Close-up view. Present for less than one week. Texture is reported as raised or bumpy. The lesion involves the head or neck. The patient is a male aged 50–59. The patient considered this a rash. No relevant systemic symptoms. The patient notes bothersome appearance, itching and enlargement:
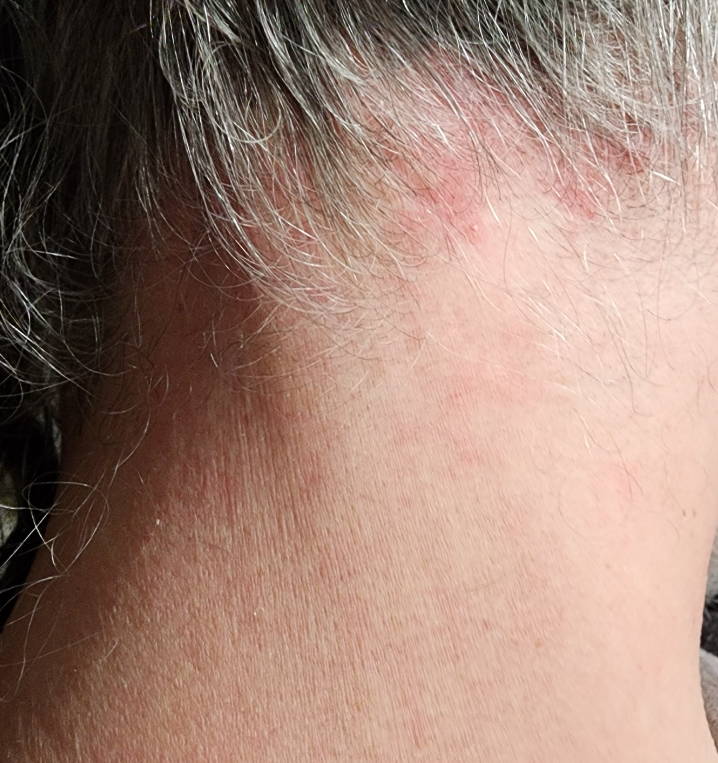On remote review of the image: Seborrheic Dermatitis (leading); Psoriasis (considered).